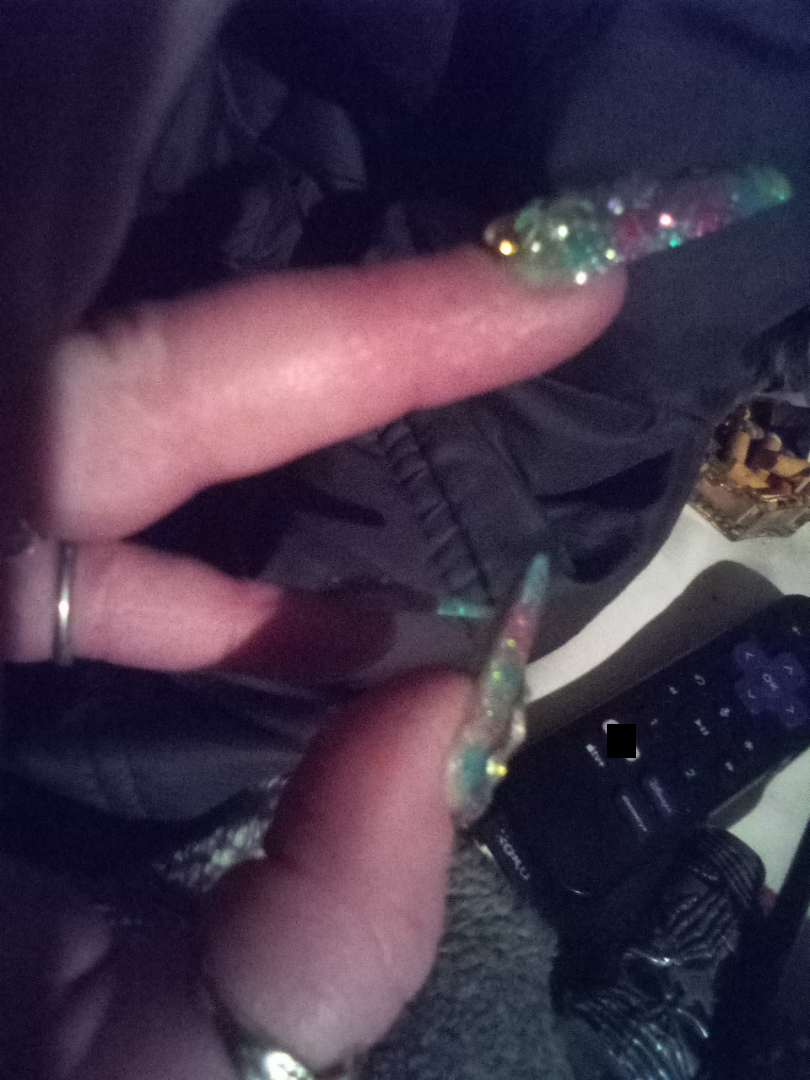Findings:
– assessment — not assessable